A dermoscopic photograph of a skin lesion:
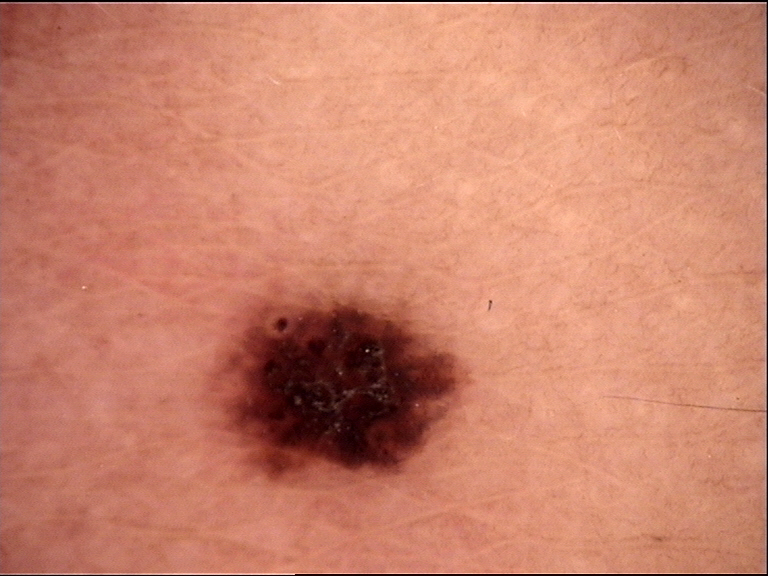Consistent with a benign lesion — a dysplastic junctional nevus.